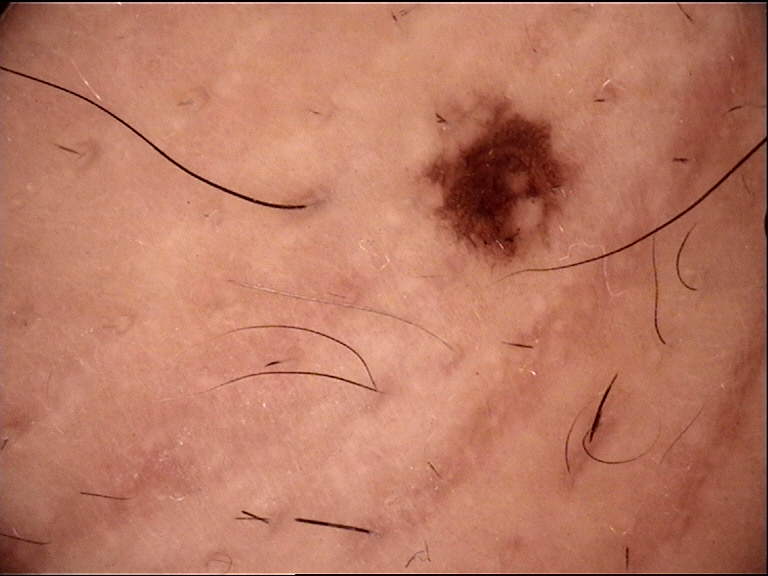Diagnosed as a compound nevus.